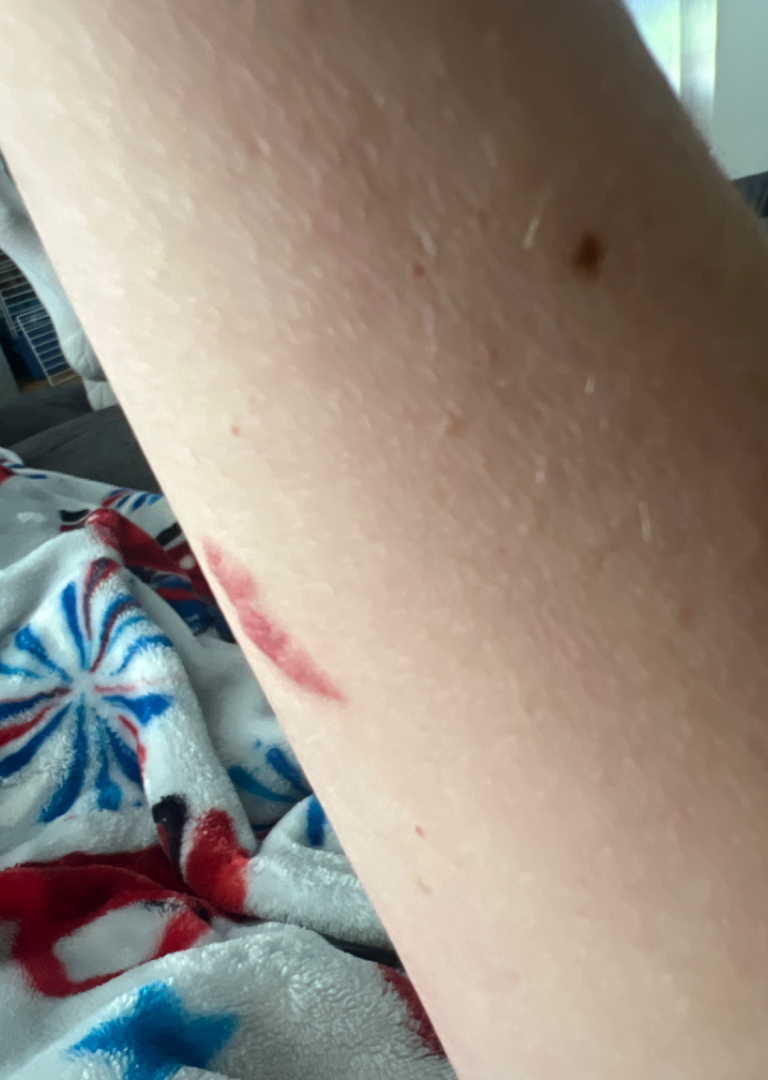Q: What was the assessment?
A: unable to determine
Q: Texture?
A: fluid-filled and raised or bumpy
Q: How was the photo taken?
A: at an angle
Q: Reported symptoms?
A: bothersome appearance and itching
Q: When did this start?
A: less than one week
Q: Fitzpatrick or Monk tone?
A: Fitzpatrick III
Q: What is the affected area?
A: arm